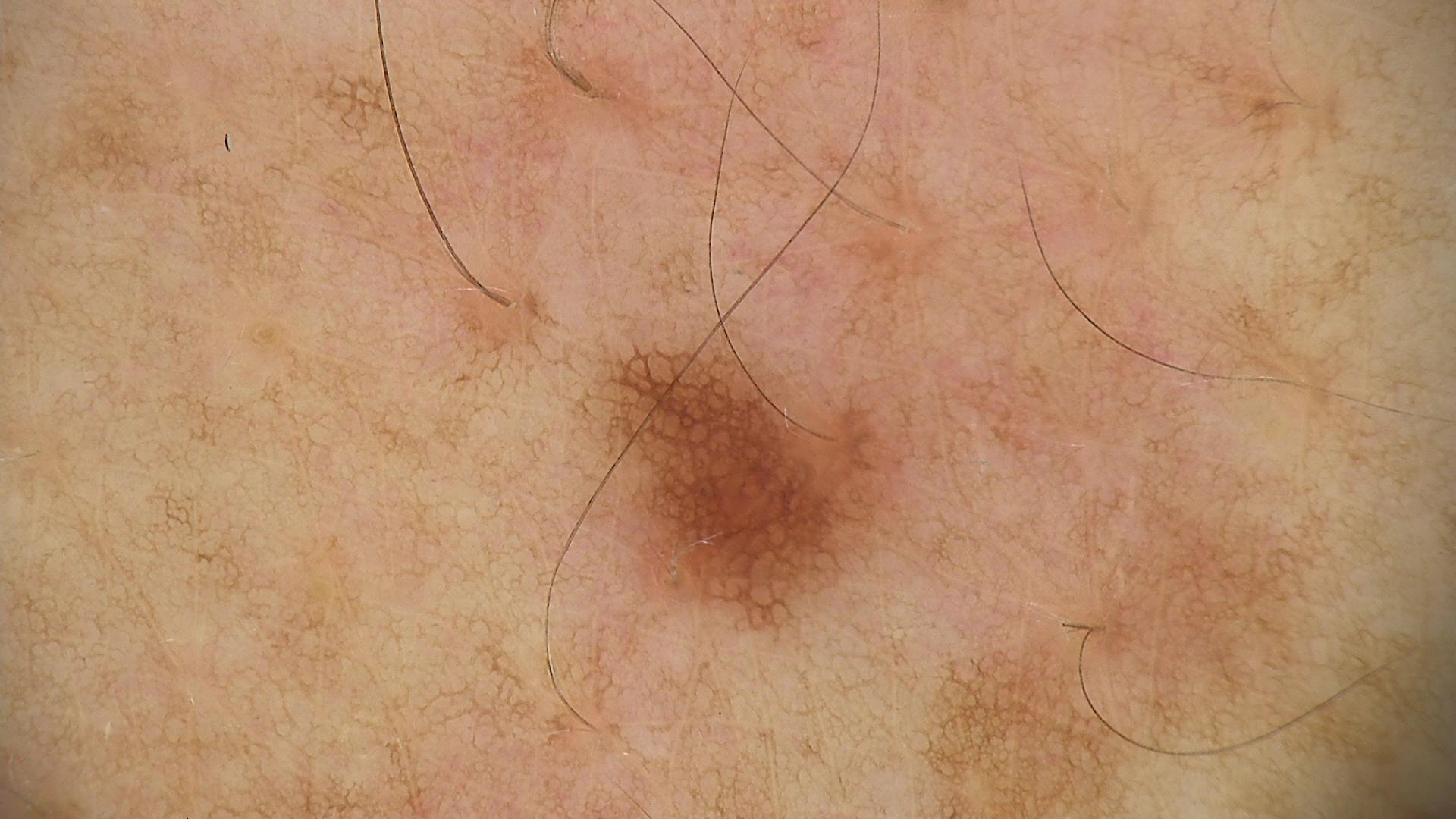diagnosis:
  name: dysplastic junctional nevus
  code: jd
  malignancy: benign
  super_class: melanocytic
  confirmation: expert consensus